A close-up photograph, the affected area is the back of the hand:
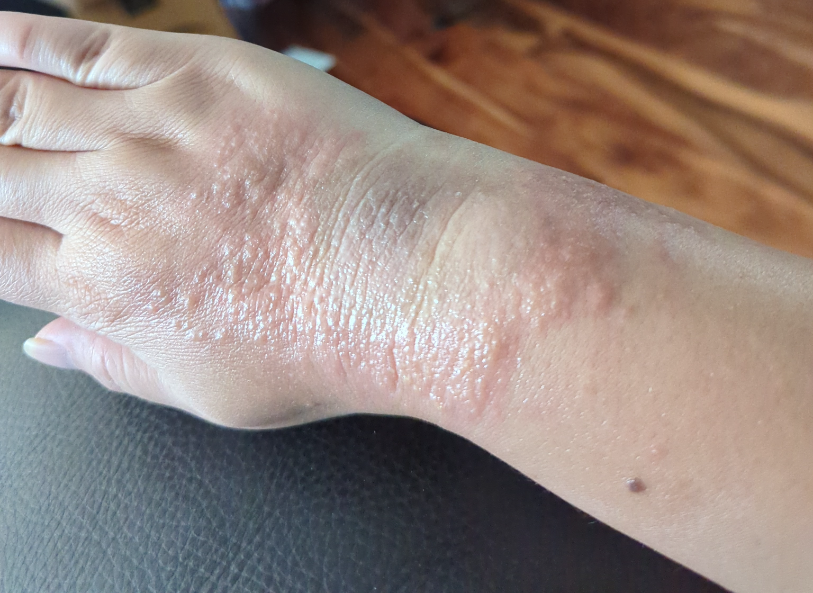patient-reported symptoms: bothersome appearance, enlargement and itching
skin tone: Fitzpatrick II; lay graders estimated a MST of 2
present for: one to three months
other reported symptoms: none reported
assessment: the impression on review was Allergic Contact Dermatitis